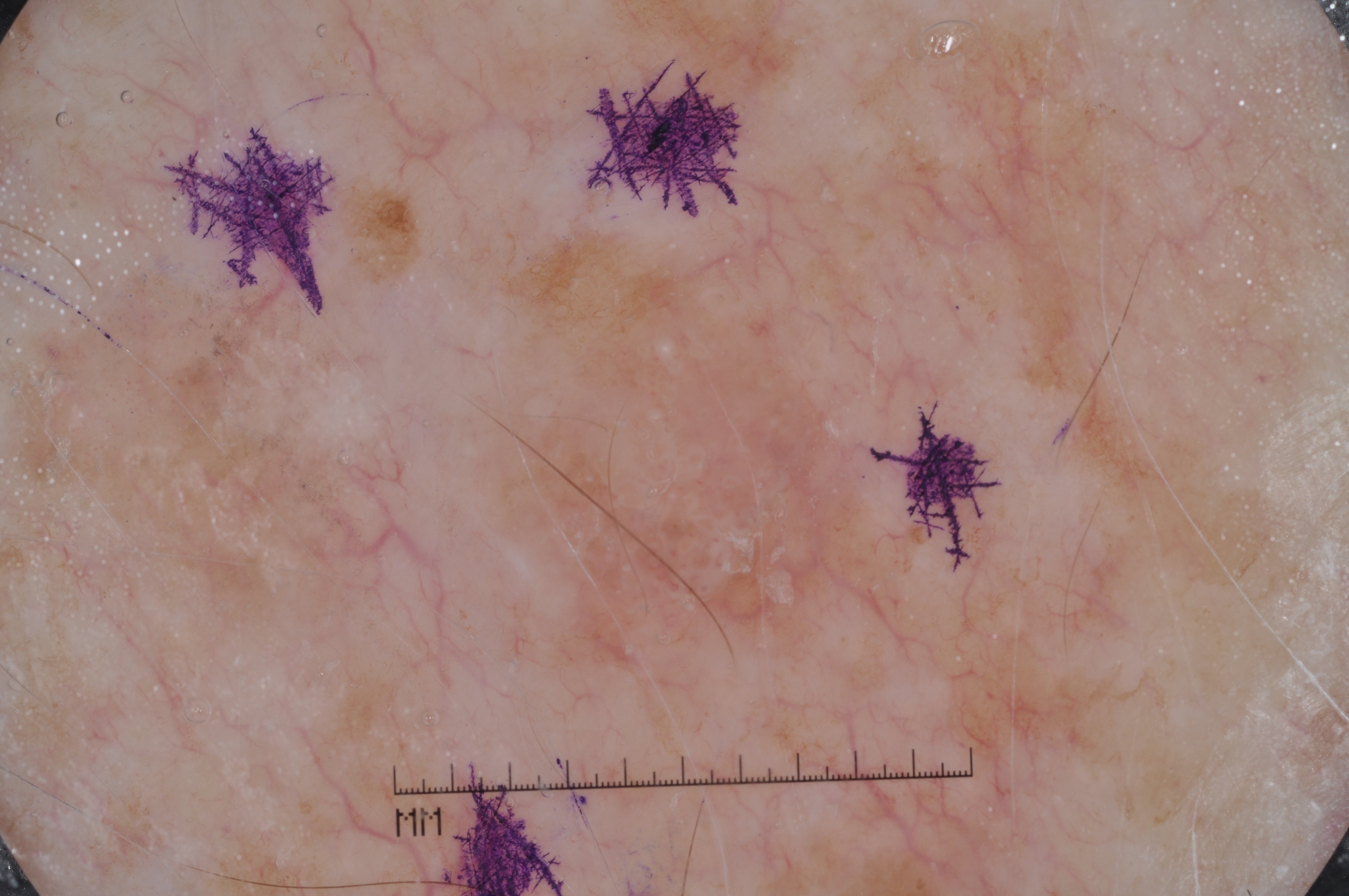Notes:
– image type · dermoscopic image
– subject · male, aged 73-77
– features · milia-like cysts and pigment network; absent: negative network and streaks
– size · large
– lesion location · x1=314 y1=165 x2=1126 y2=845
– diagnostic label · a seborrheic keratosis, a benign lesion